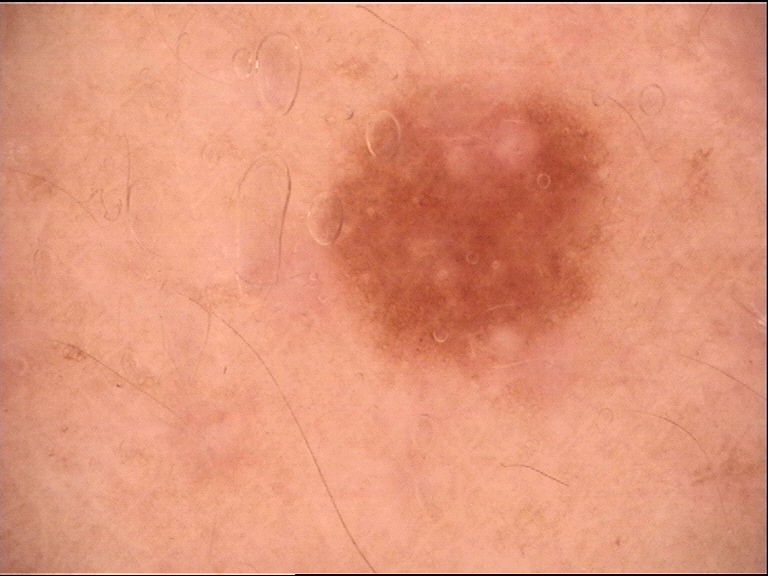A dermoscopic image of a skin lesion.
Diagnosed as a dysplastic junctional nevus.